A skin lesion imaged with a dermatoscope:
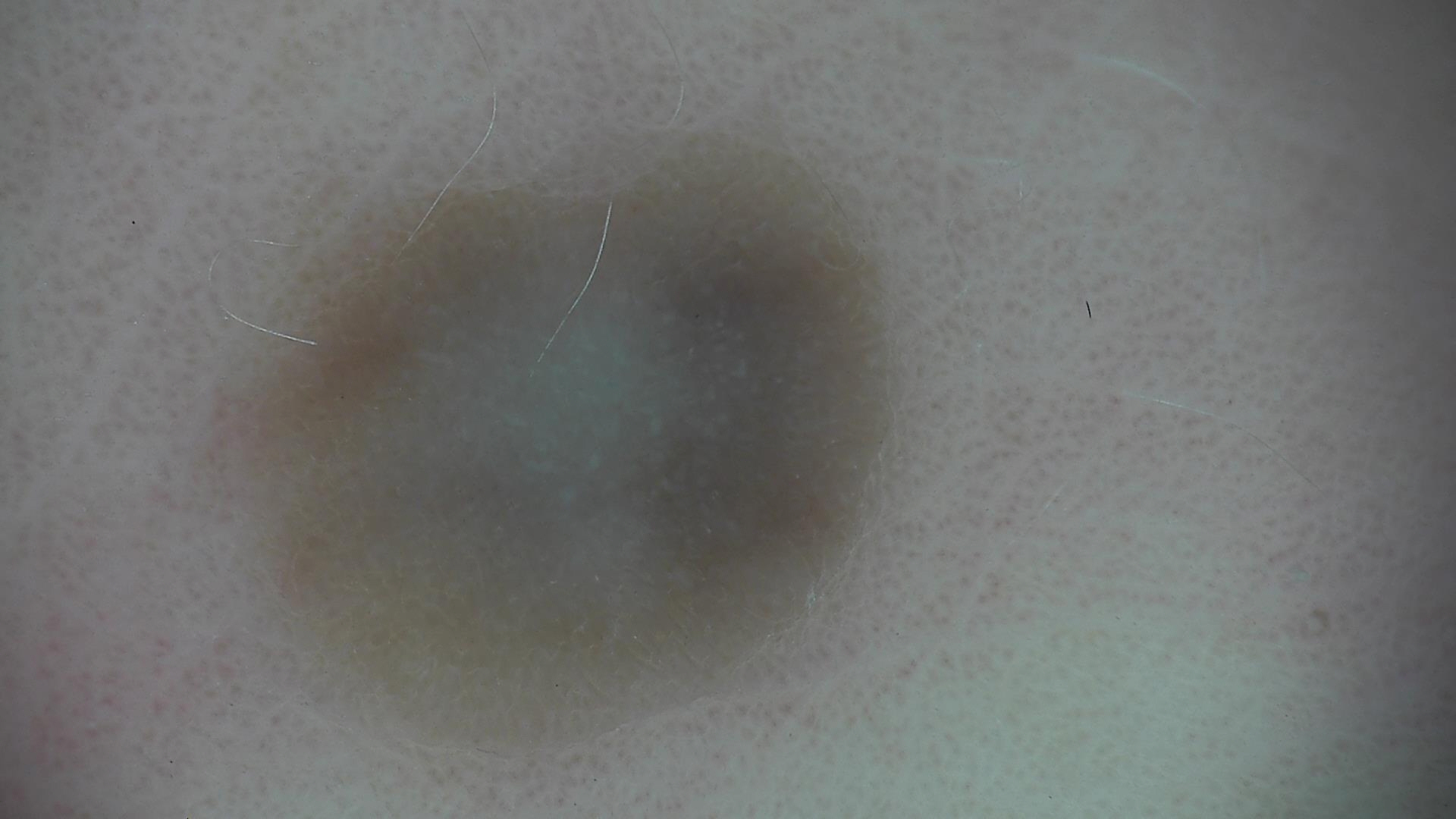Case: This is a banal, dermal lesion. Conclusion: Consistent with a blue nevus.